Recorded as skin type III; a dermoscopic photograph of a skin lesion; a female subject aged approximately 30.
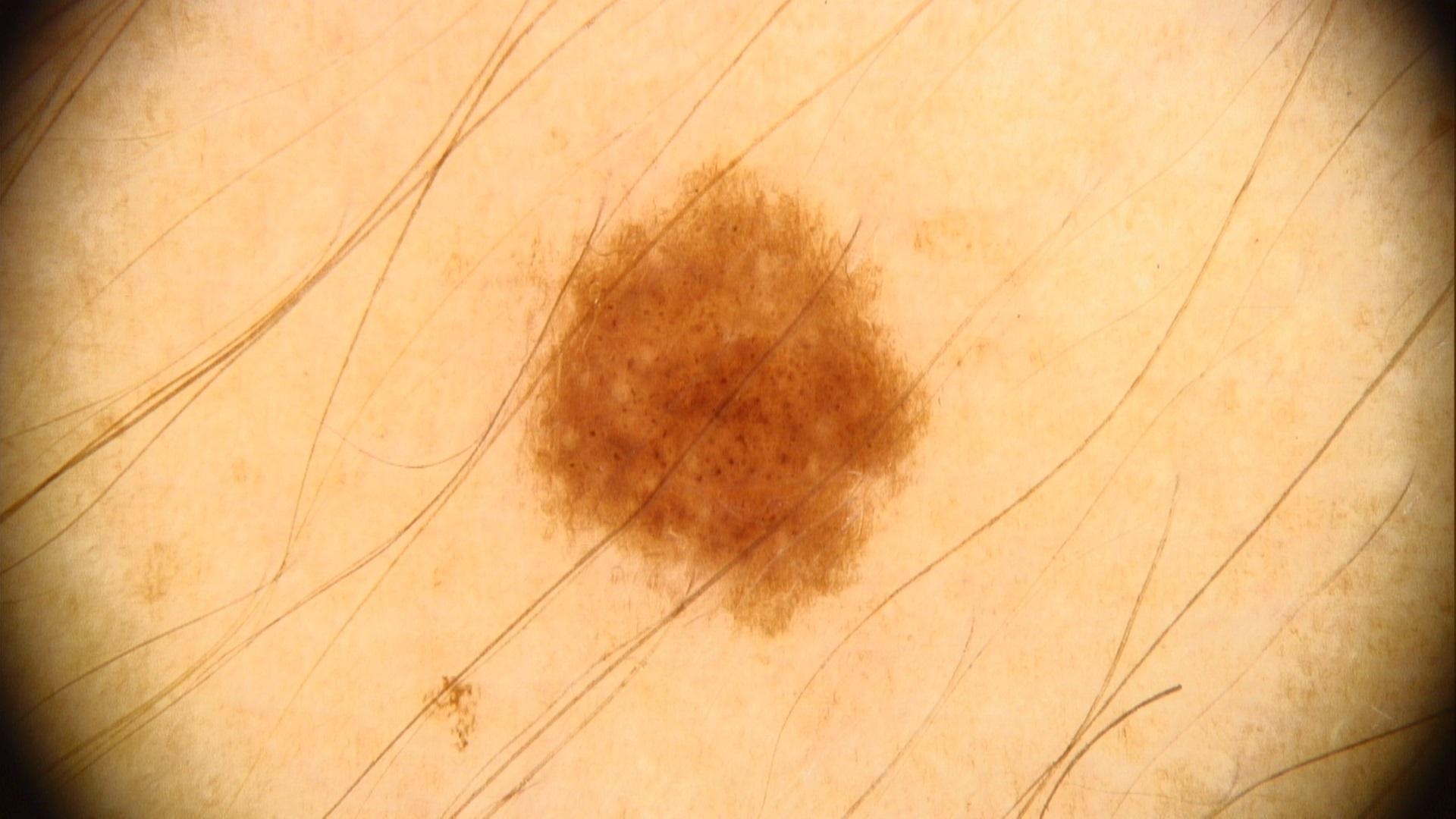Findings: The lesion involves an upper extremity. Assessment: The clinical impression was a benign, melanocytic lesion — a nevus.